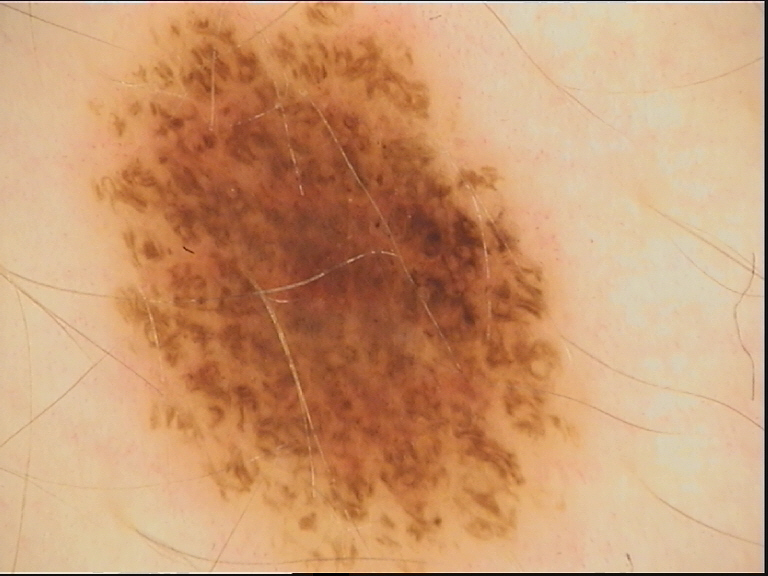image type=dermatoscopy
diagnosis=dysplastic compound nevus (expert consensus)